The patient is a male aged 18–29, present for less than one week, reported lesion symptoms include bothersome appearance, the contributor notes the lesion is raised or bumpy and fluid-filled, an image taken at an angle, self-categorized by the patient as a rash, skin tone: Fitzpatrick phototype IV, the front of the torso is involved.
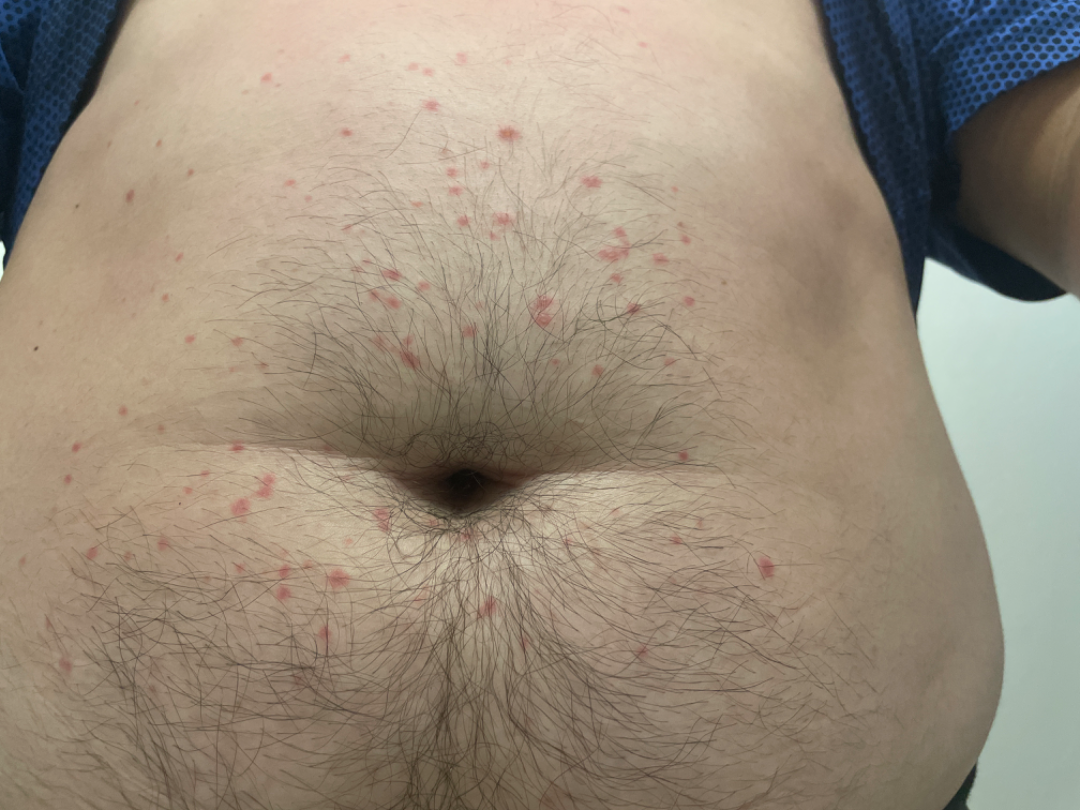{
  "assessment": "unable to determine"
}